The subject is a female aged 70–79 · skin tone: Fitzpatrick III; non-clinician graders estimated 2 on the MST · the contributor notes the condition has been present for less than one week · the affected area is the leg · this image was taken at a distance · self-categorized by the patient as a rash — 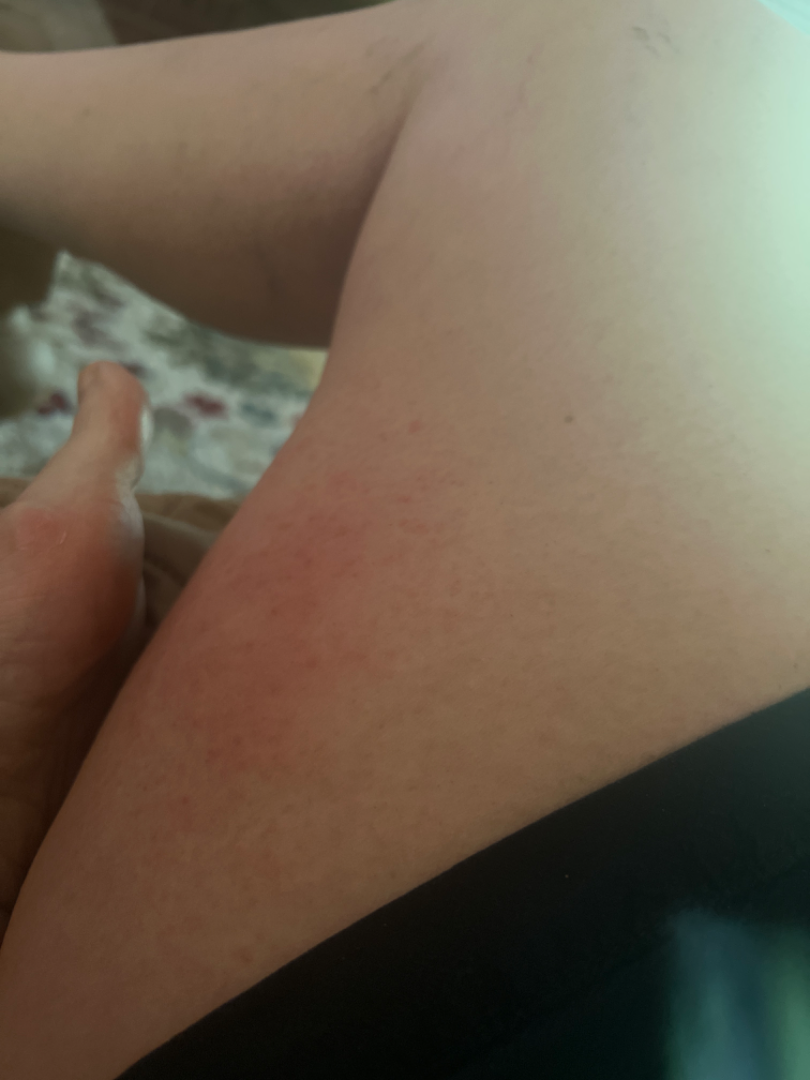On remote dermatologist review: the primary impression is Eczema; an alternative is Allergic Contact Dermatitis.